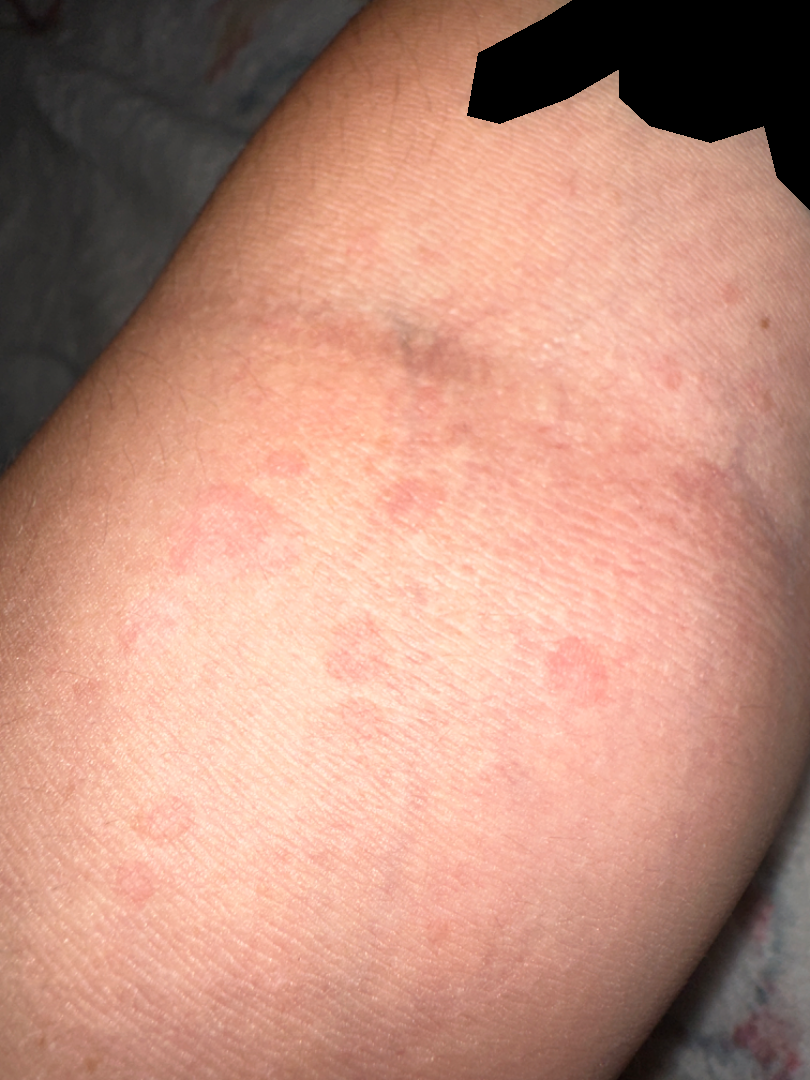Case summary:
- reported symptoms — none reported
- lesion texture — flat
- present for — about one day
- shot type — at a distance
- patient — female, age 18–29
- body site — arm
- differential diagnosis — most consistent with Tinea Versicolor; also consider Urticaria; less probable is Eczema; a more distant consideration is Insect Bite; less likely is Psoriasis